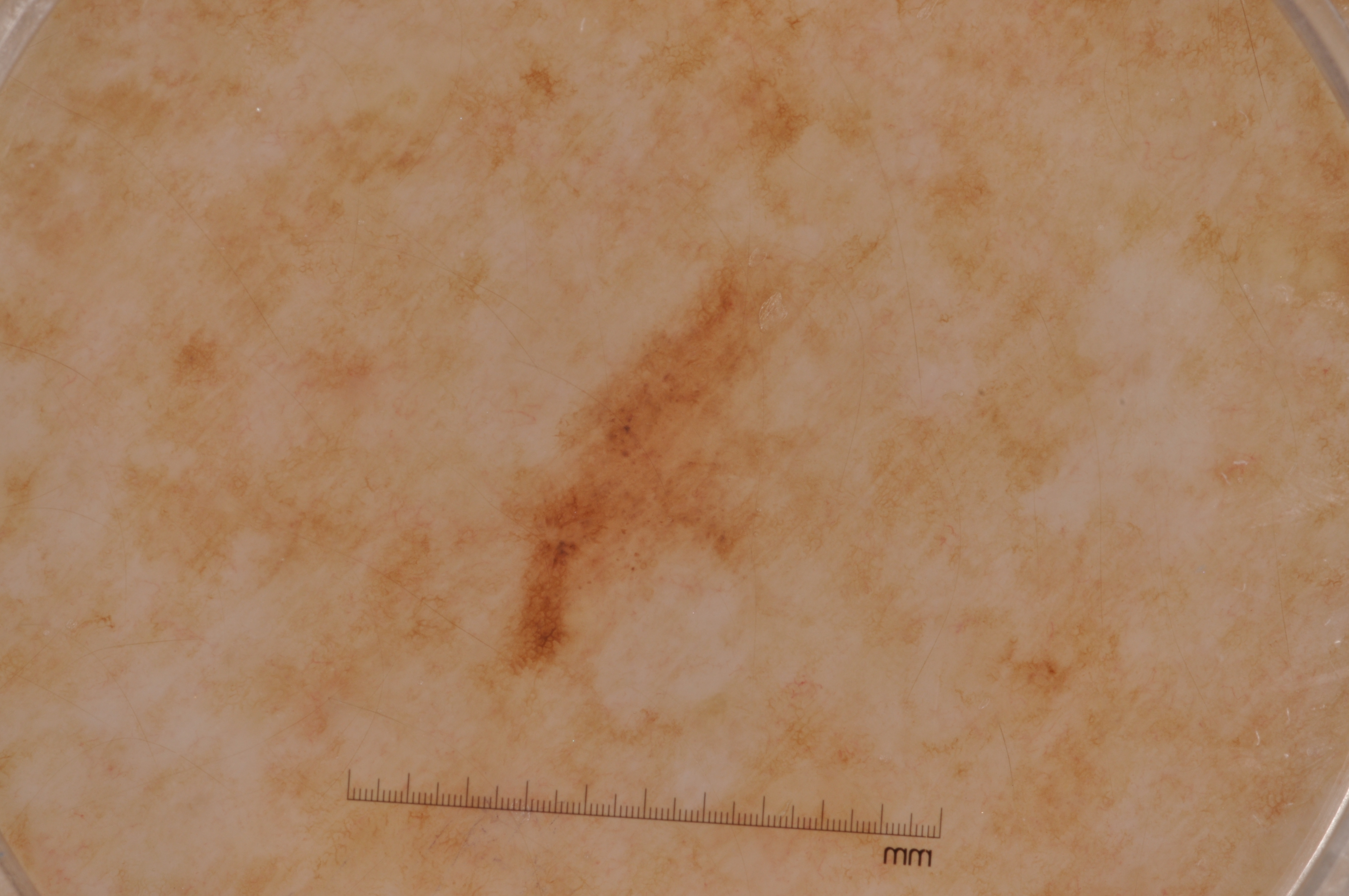Findings:
The subject is a female aged 53-57. A dermoscopic close-up of a skin lesion. On dermoscopy, the lesion shows pigment network, with no milia-like cysts, streaks, or negative network. In (x1, y1, x2, y2) order, the lesion spans bbox=[469, 244, 800, 695].
Assessment:
The clinical diagnosis was a melanocytic nevus.